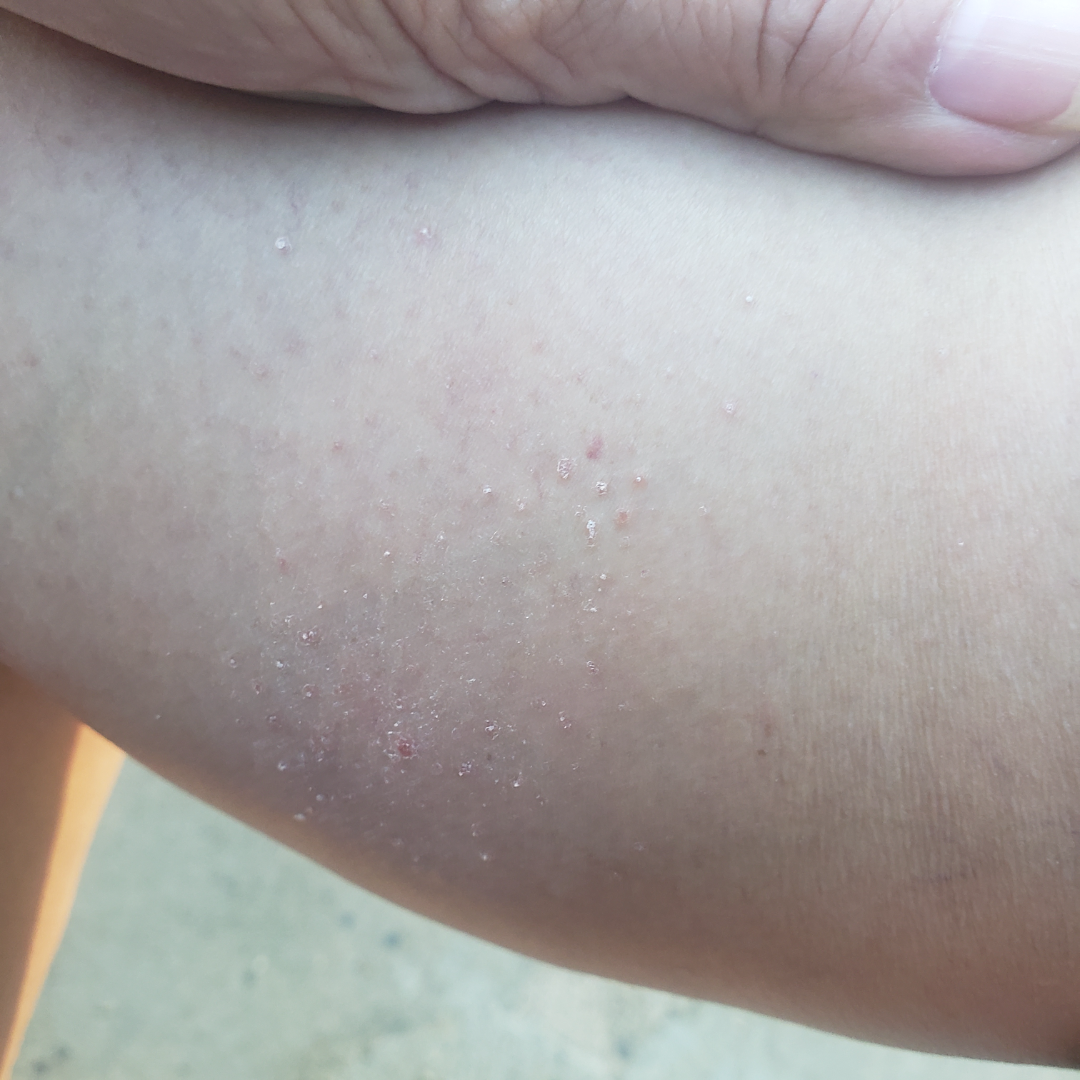A close-up photograph.
Located on the arm and leg.
On remote dermatologist review: Keratosis pilaris and Lichen spinulosus were considered with similar weight; less likely is Xerosis.